Self-categorized by the patient as a rash. The patient indicates the lesion is raised or bumpy. Symptoms reported: enlargement. The photograph was taken at a distance — 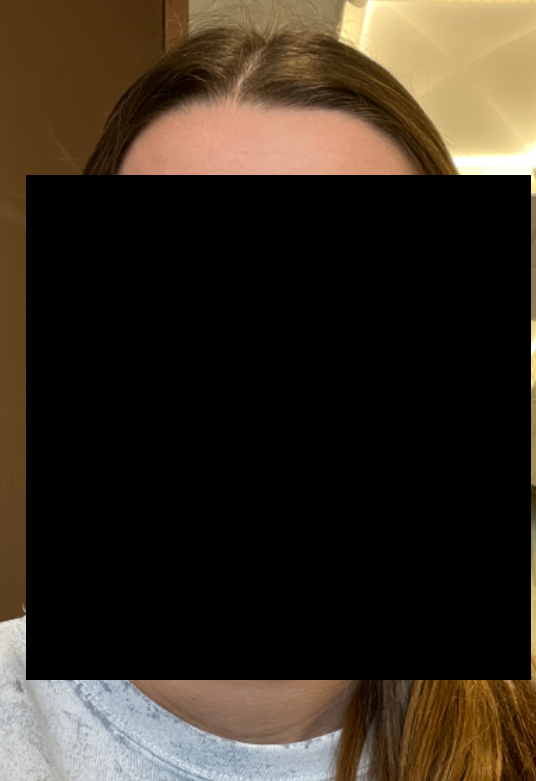<report>
  <differential>
    <Acne>0.55</Acne>
    <Rosacea>0.27</Rosacea>
    <Folliculitis>0.18</Folliculitis>
  </differential>
</report>